A wide-field clinical photograph of a skin lesion. A female patient aged 63-67 — 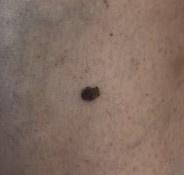lesion_location:
  region: a lower extremity
diagnosis:
  name: Melanoma
  malignancy: malignant
  confirmation: histopathology